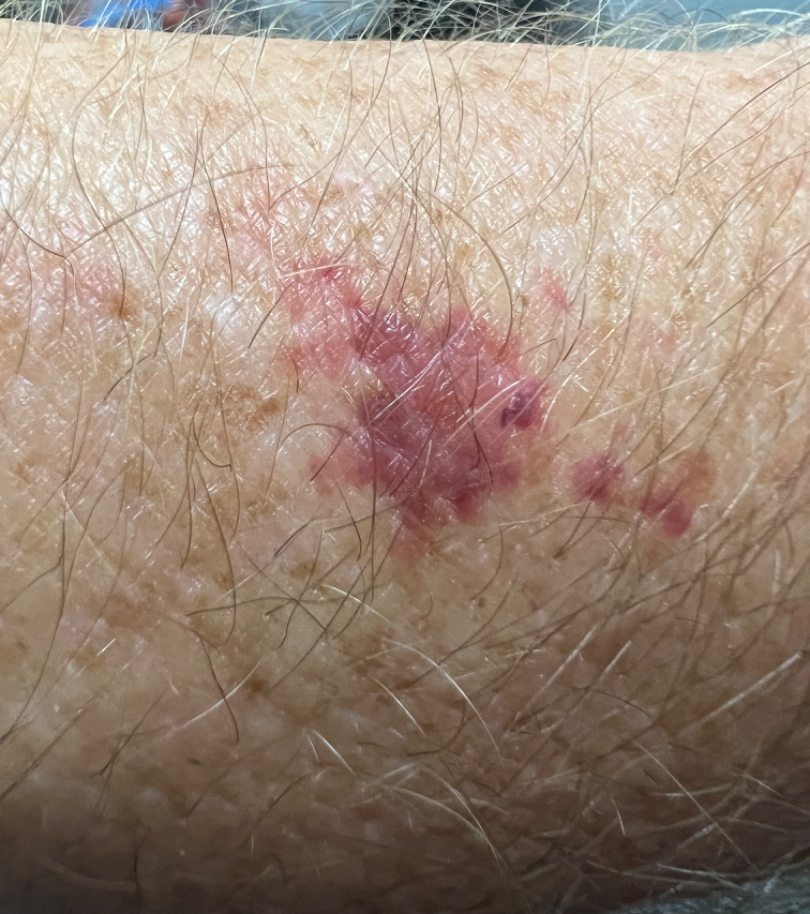The lesion is described as flat.
The arm is involved.
The contributor is a male aged 60–69.
A close-up photograph.
The patient described the issue as a rash.
No associated lesion symptoms were reported.
Reported duration is about one day.
Lay graders estimated 3 on the Monk Skin Tone.
On teledermatology review, most consistent with ecchymoses.